A female patient aged 33-37. The patient is skin type II.
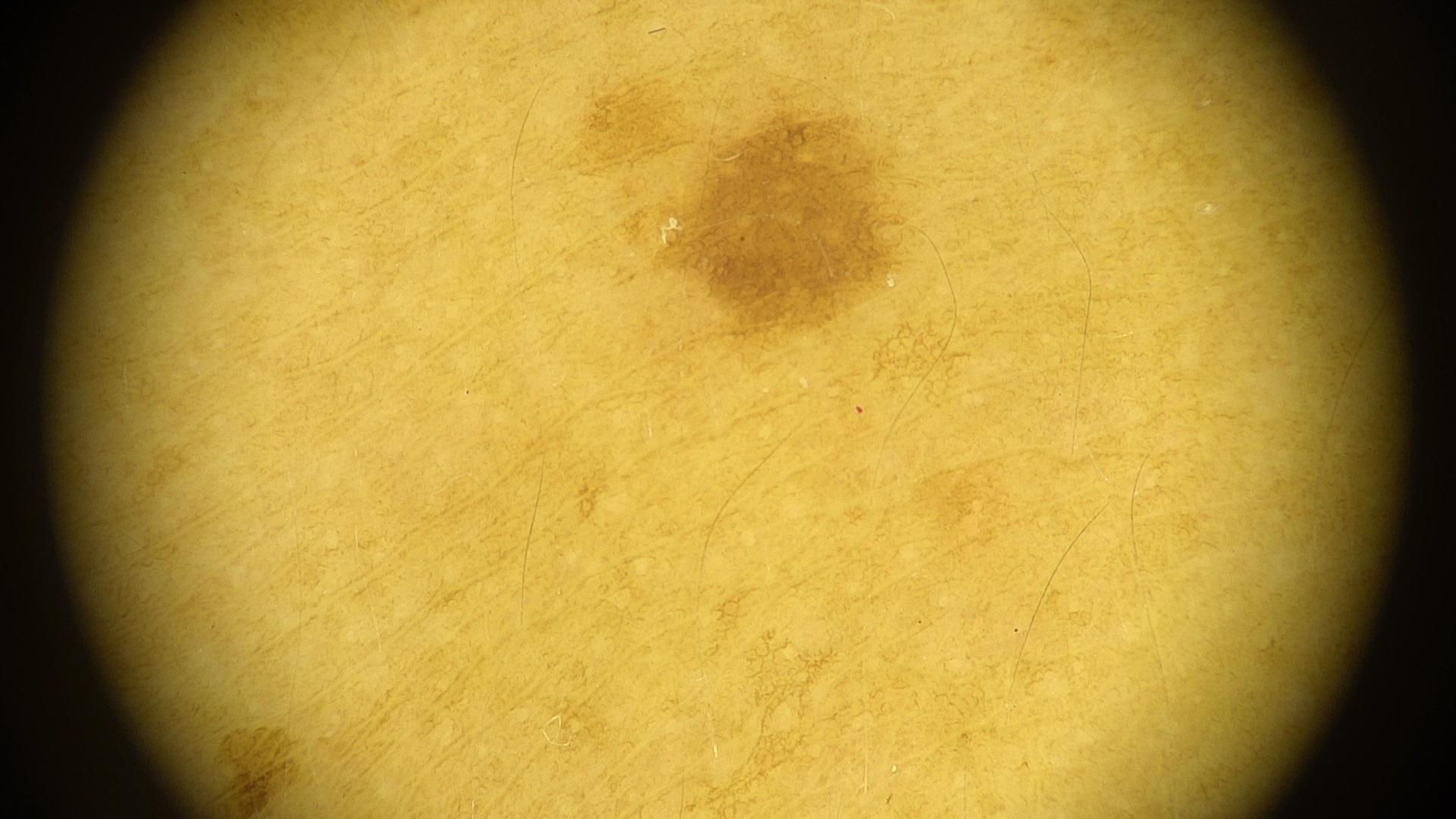The lesion involves an upper extremity. The clinical assessment was a melanocytic lesion — a nevus.